Close-up view — 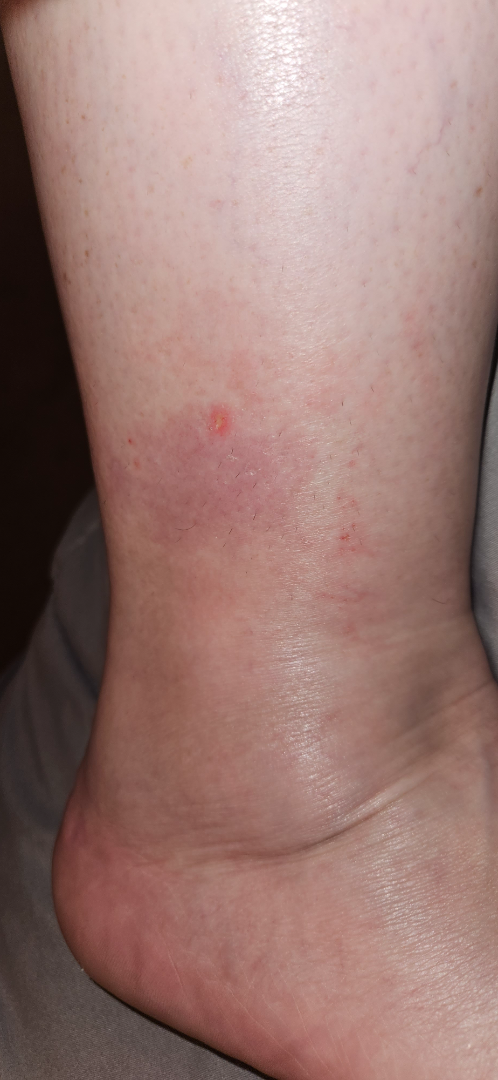On dermatologist assessment of the image, Stasis Dermatitis (0.67); Livedoid vasculopathy (0.33).